A dermatoscopic image of a skin lesion.
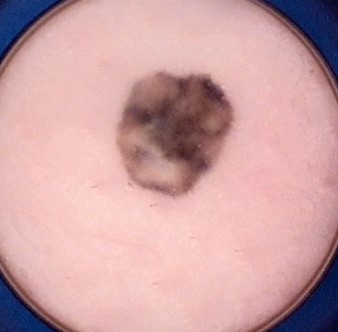Impression: Diagnosed as a banal lesion — a blue nevus.